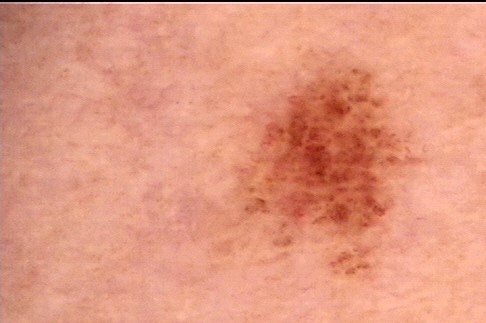Classified as a junctional nevus.